The patient described the issue as a nail problem · Fitzpatrick skin type II; lay graders estimated Monk Skin Tone 2 · the condition has been present for more than five years · male subject, age 50–59 · the patient did not report lesion symptoms · texture is reported as rough or flaky · an image taken at a distance · the affected area is the top or side of the foot:
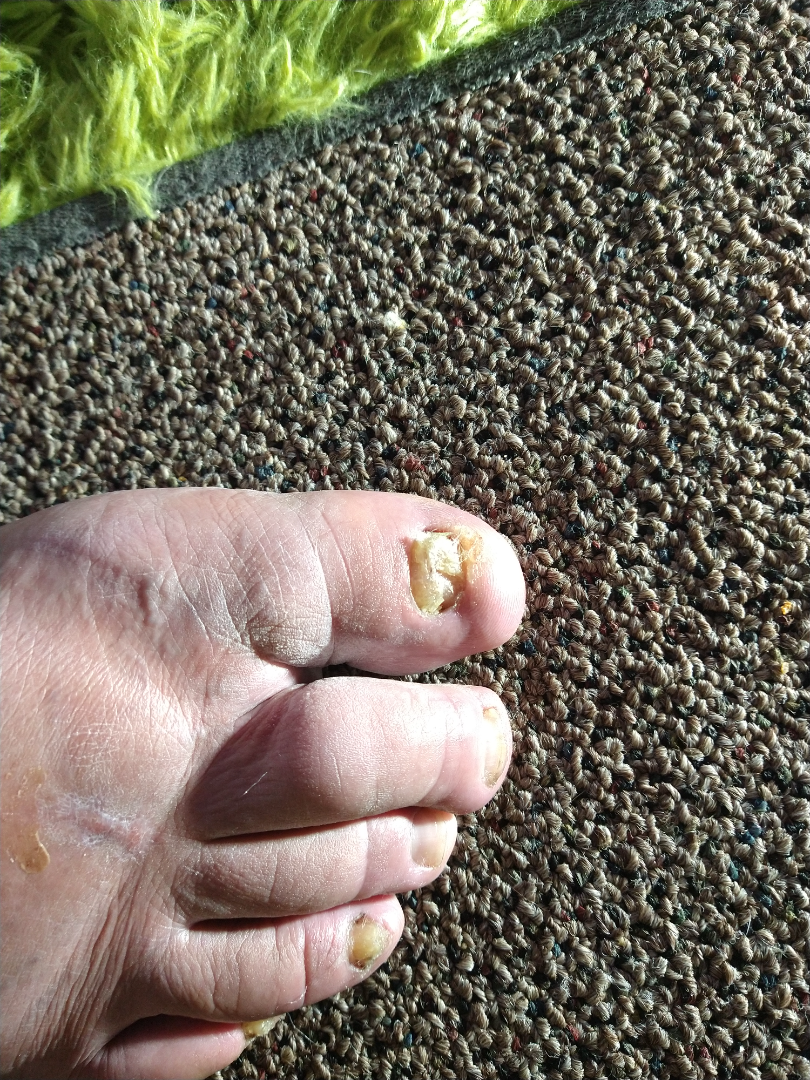Favoring Onychomycosis; lower on the differential is Verruca vulgaris; a more distant consideration is Psoriasis; less probable is Nail dystrophy due to trauma.